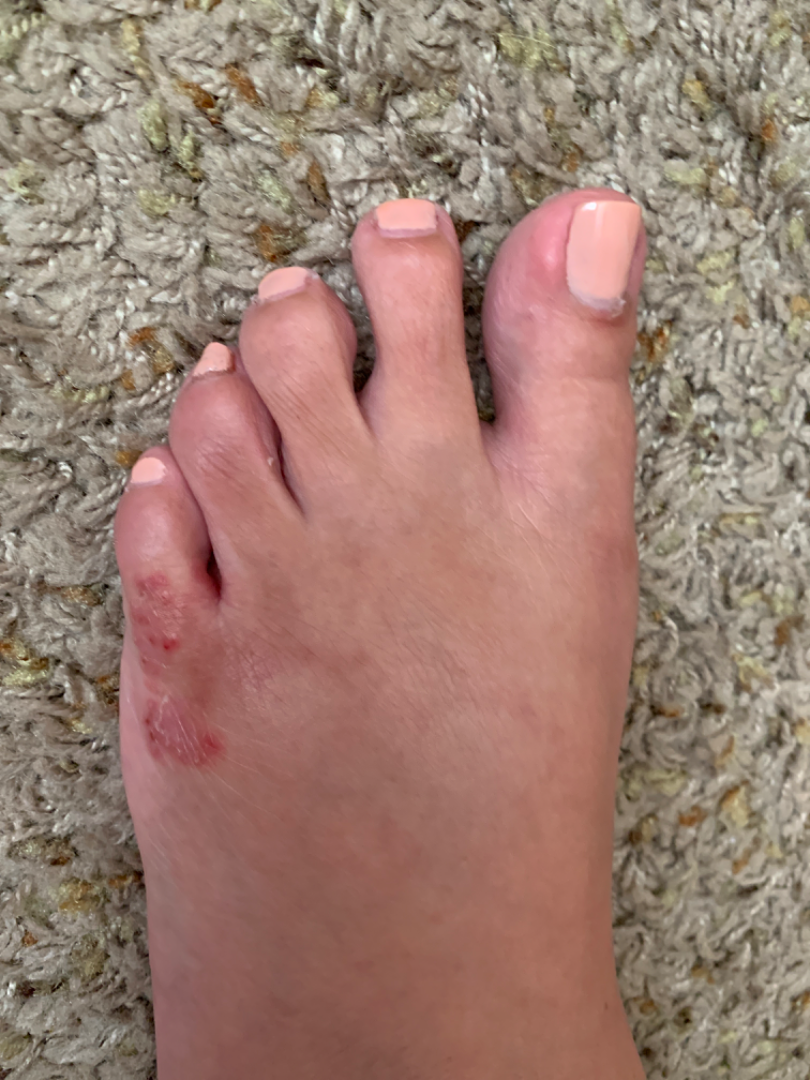Lay reviewers estimated Monk Skin Tone 3 or 5 (two reviewer pools disagreed). A close-up photograph. The reviewing clinician's impression was: Eczema and Allergic Contact Dermatitis were considered with similar weight.